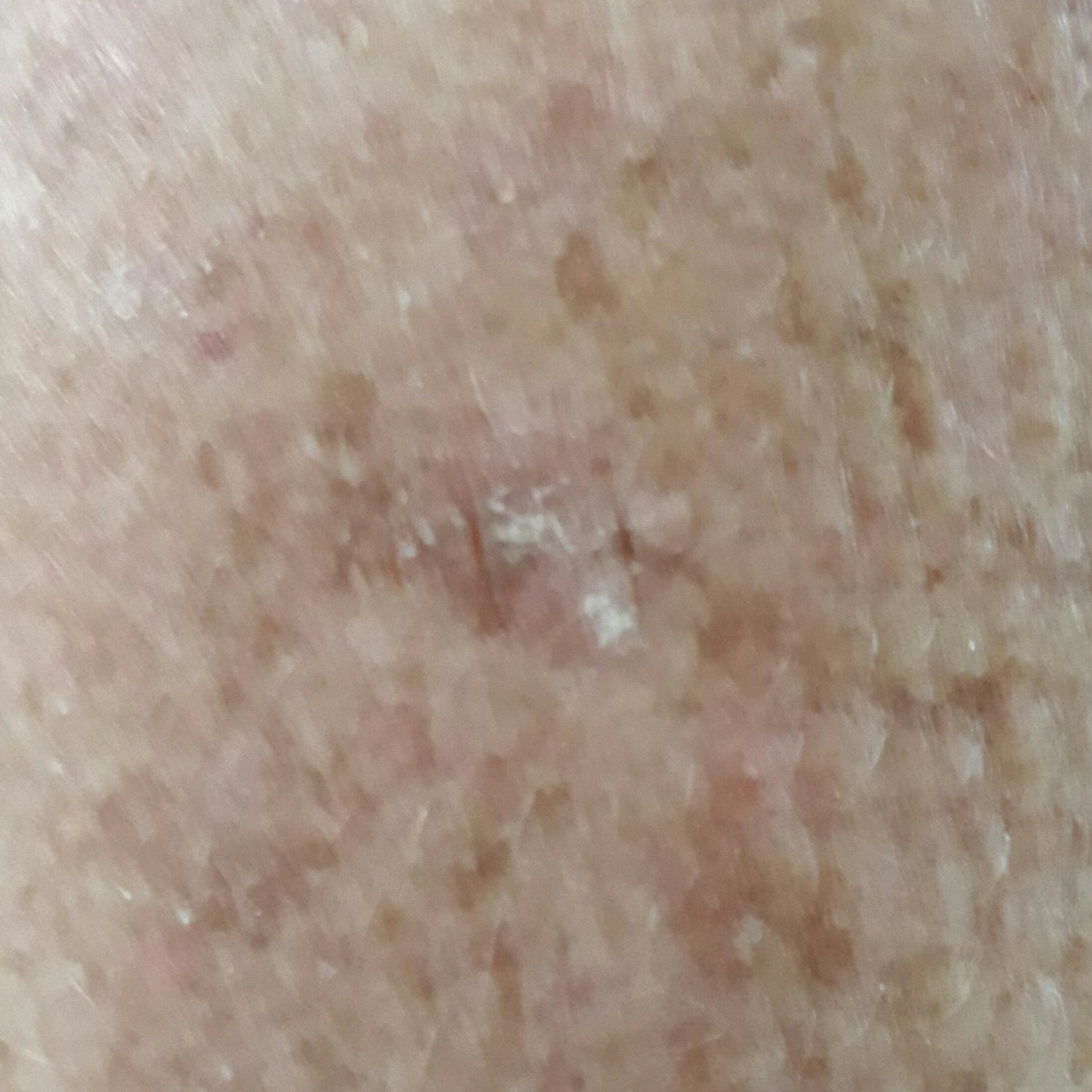subject: 60 years old, symptoms: growth, impression: actinic keratosis (clinical consensus).